A female subject aged approximately 35, this is a dermoscopic photograph of a skin lesion — 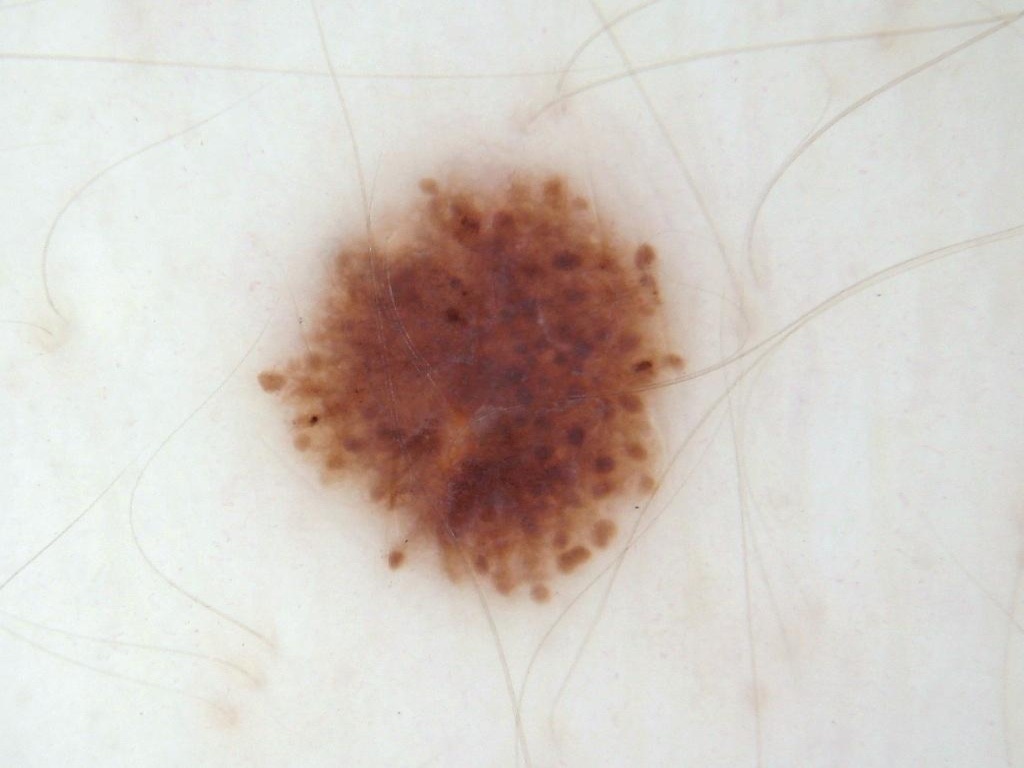dermoscopic pattern: globules | extent: ~19% of the field | bounding box: 250 160 697 615 | impression: a melanocytic nevus, a benign skin lesion.